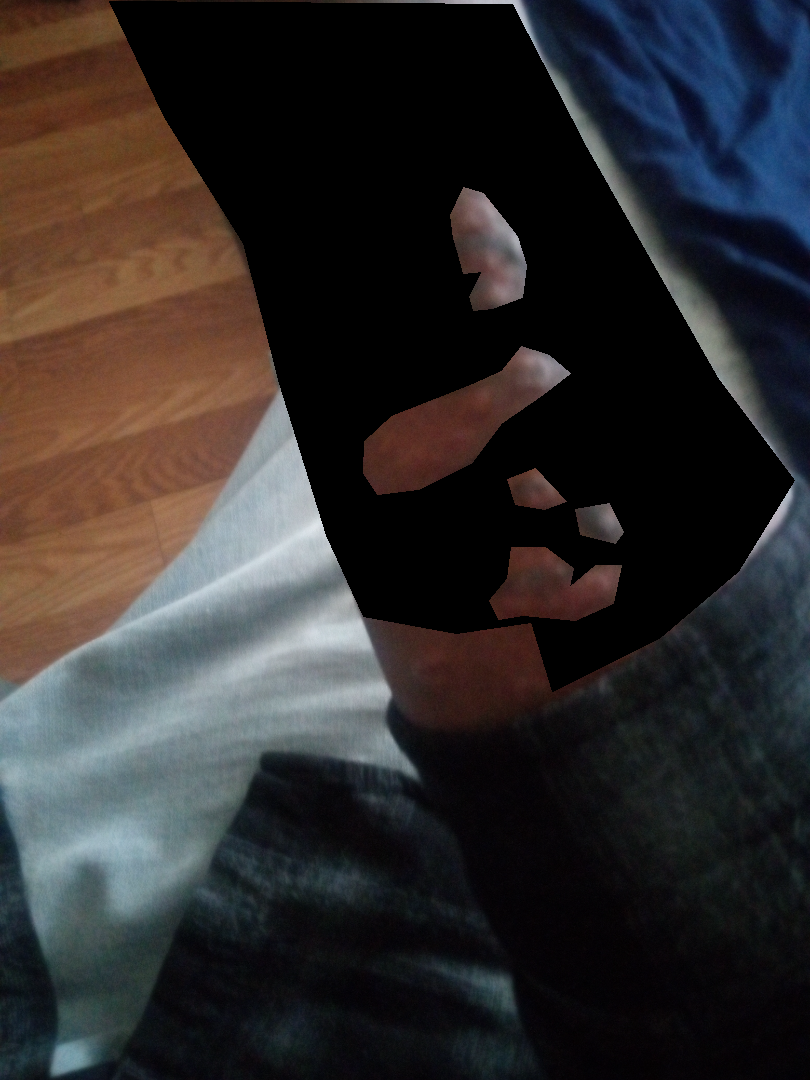Assessment:
On remote review of the image, the differential is split between Cutaneous T Cell Lymphoma, Kaposi's sarcoma of skin and Lichen planus/lichenoid eruption.